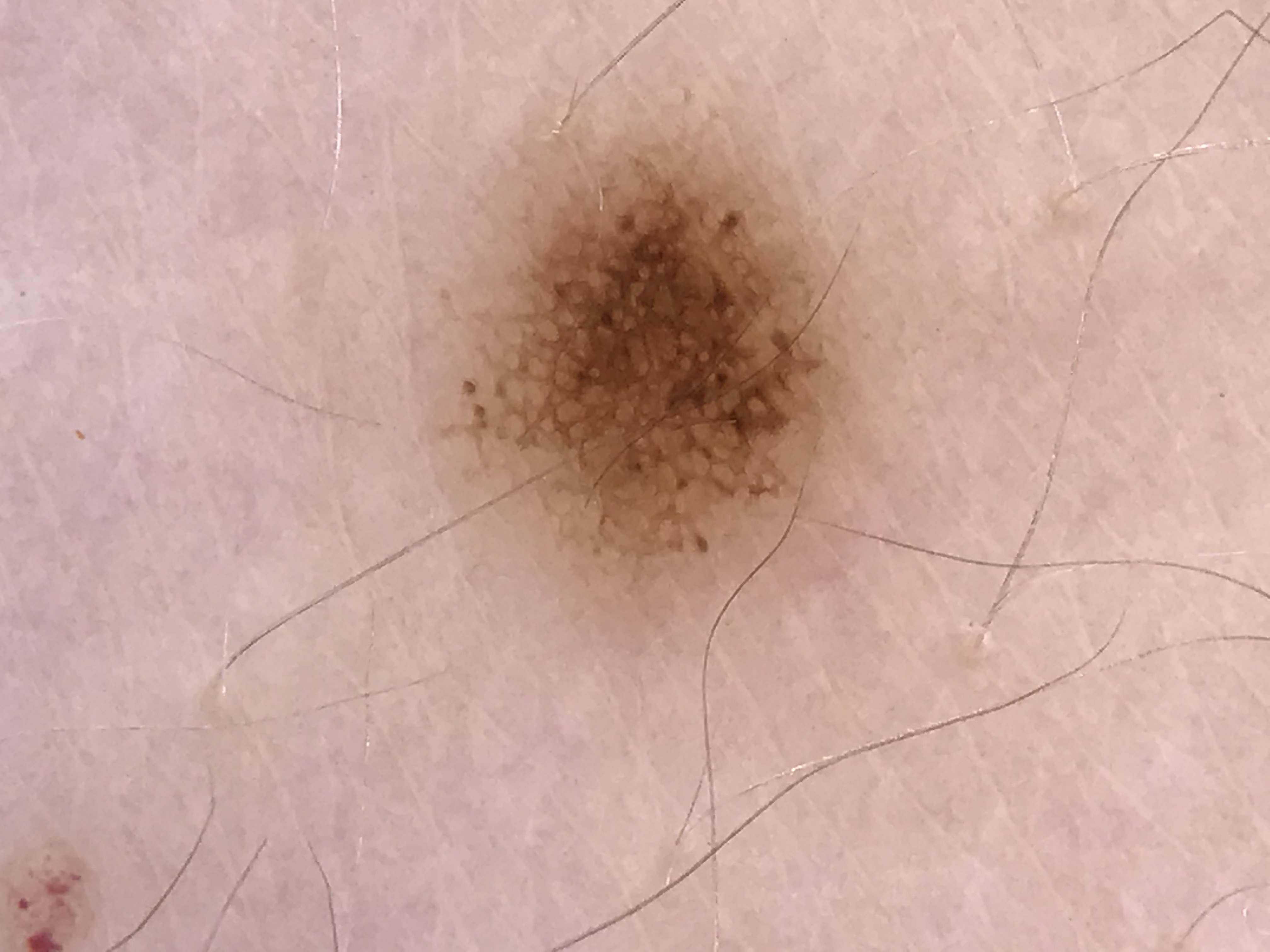A dermatoscopic image of a skin lesion. Labeled as a dysplastic junctional nevus.